A clinical photograph showing a skin lesion. A subject age 81.
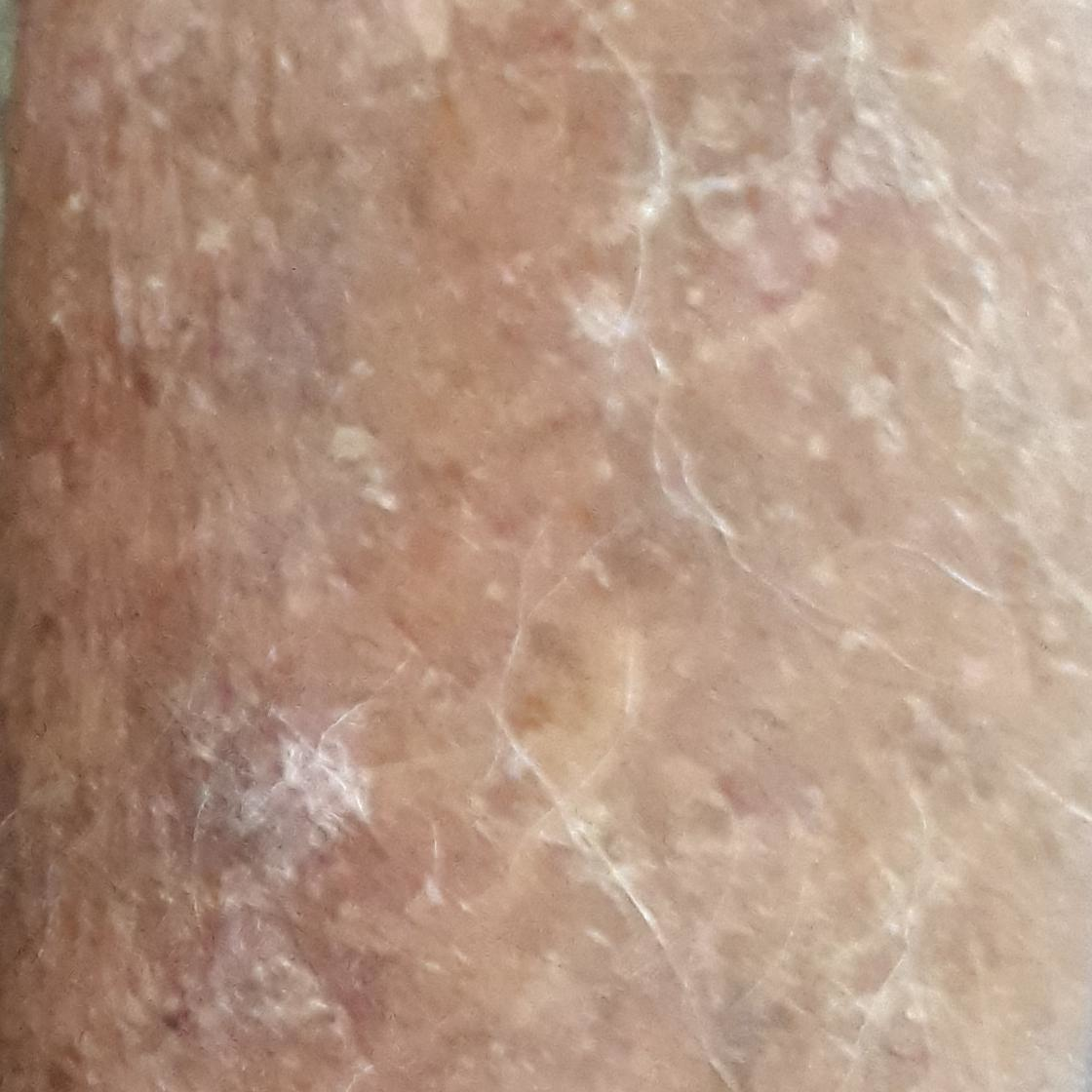The lesion involves a forearm. By the patient's account, the lesion itches, but is not elevated and has not grown. The diagnostic impression was an actinic keratosis.